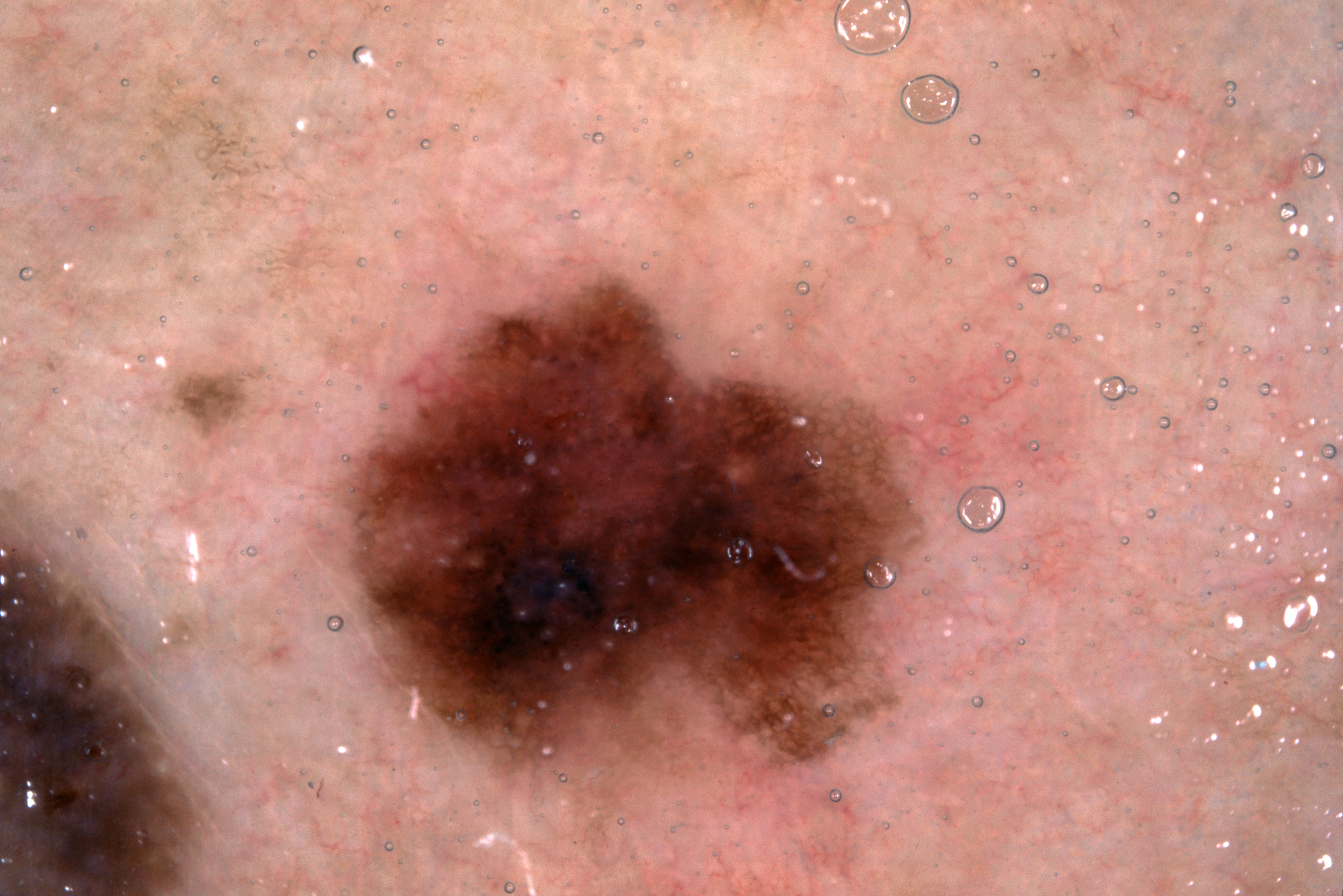subject = female, about 70 years old
modality = dermoscopic image
dermoscopic pattern = milia-like cysts and pigment network; absent: negative network and streaks
lesion extent = moderate
lesion bbox = [357,287,912,763]
impression = a melanoma, a malignant skin lesion